A dermoscopic photograph of a skin lesion: 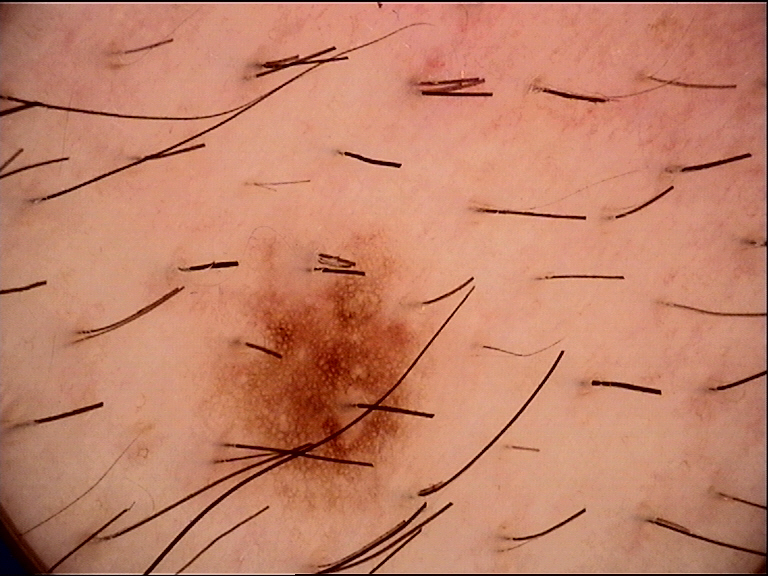The diagnostic label was a dysplastic junctional nevus.